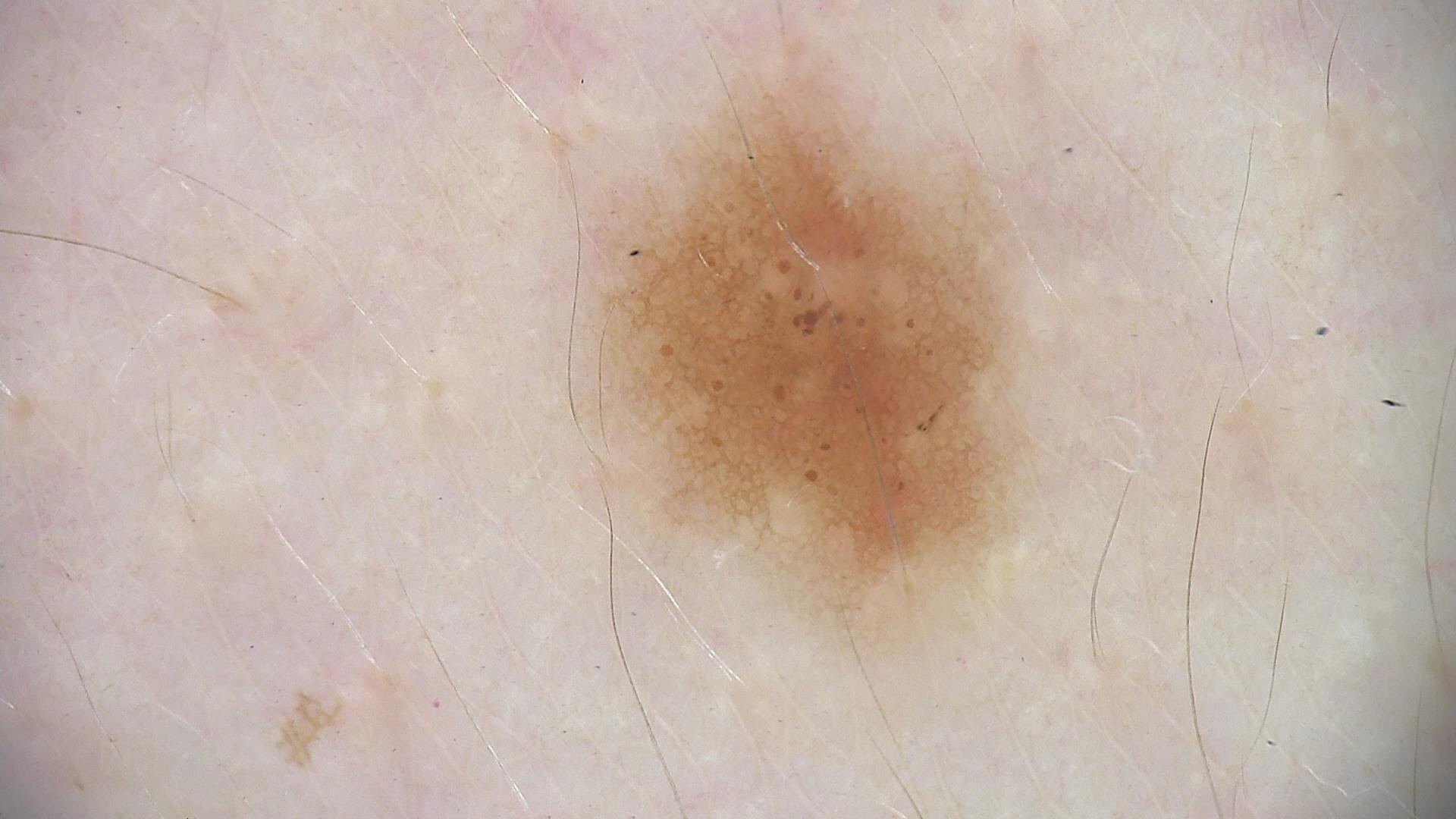Consistent with a dysplastic junctional nevus.